A dermoscopic photograph of a skin lesion.
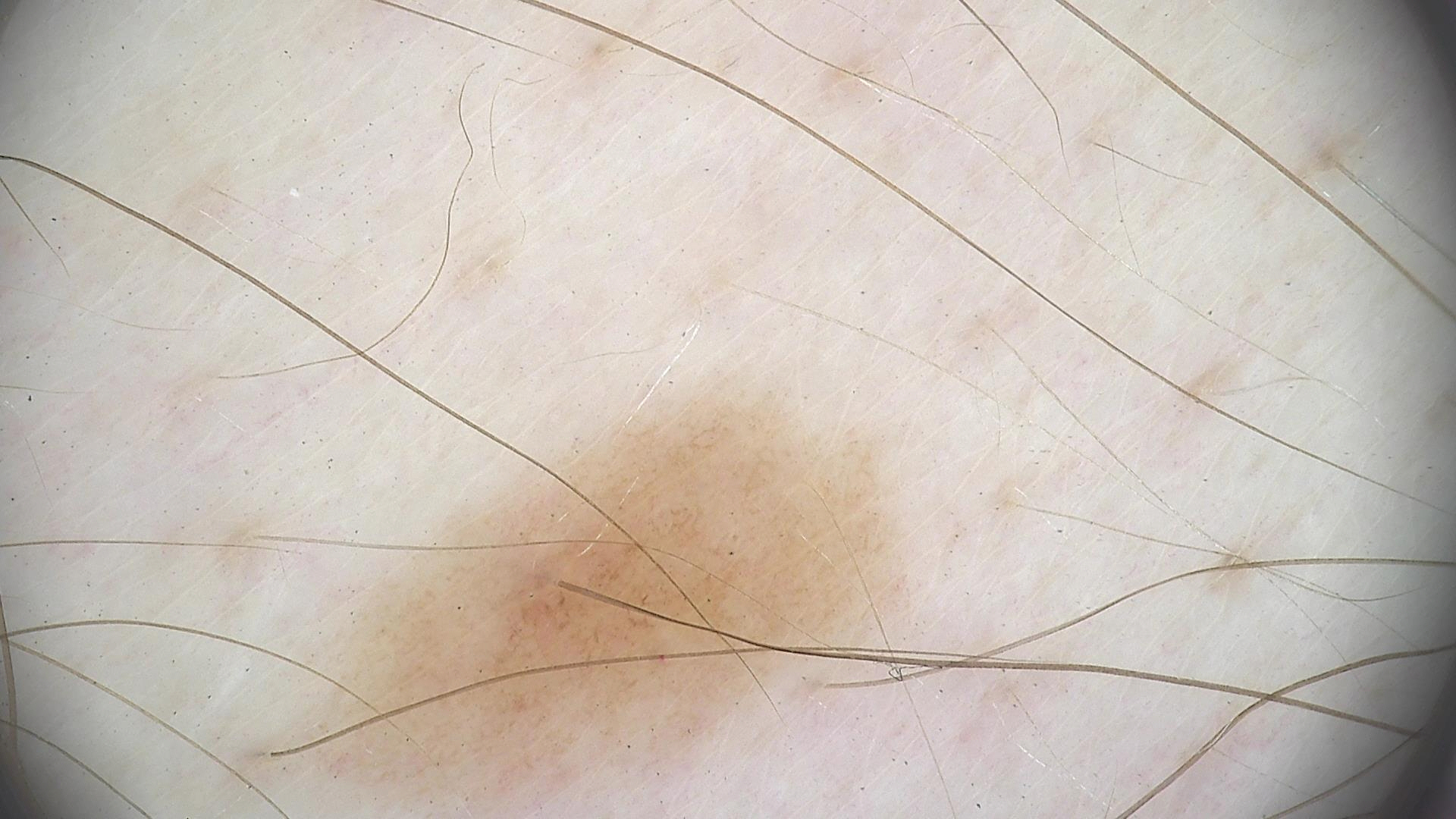  diagnosis:
    name: dysplastic junctional nevus
    code: jd
    malignancy: benign
    super_class: melanocytic
    confirmation: expert consensus